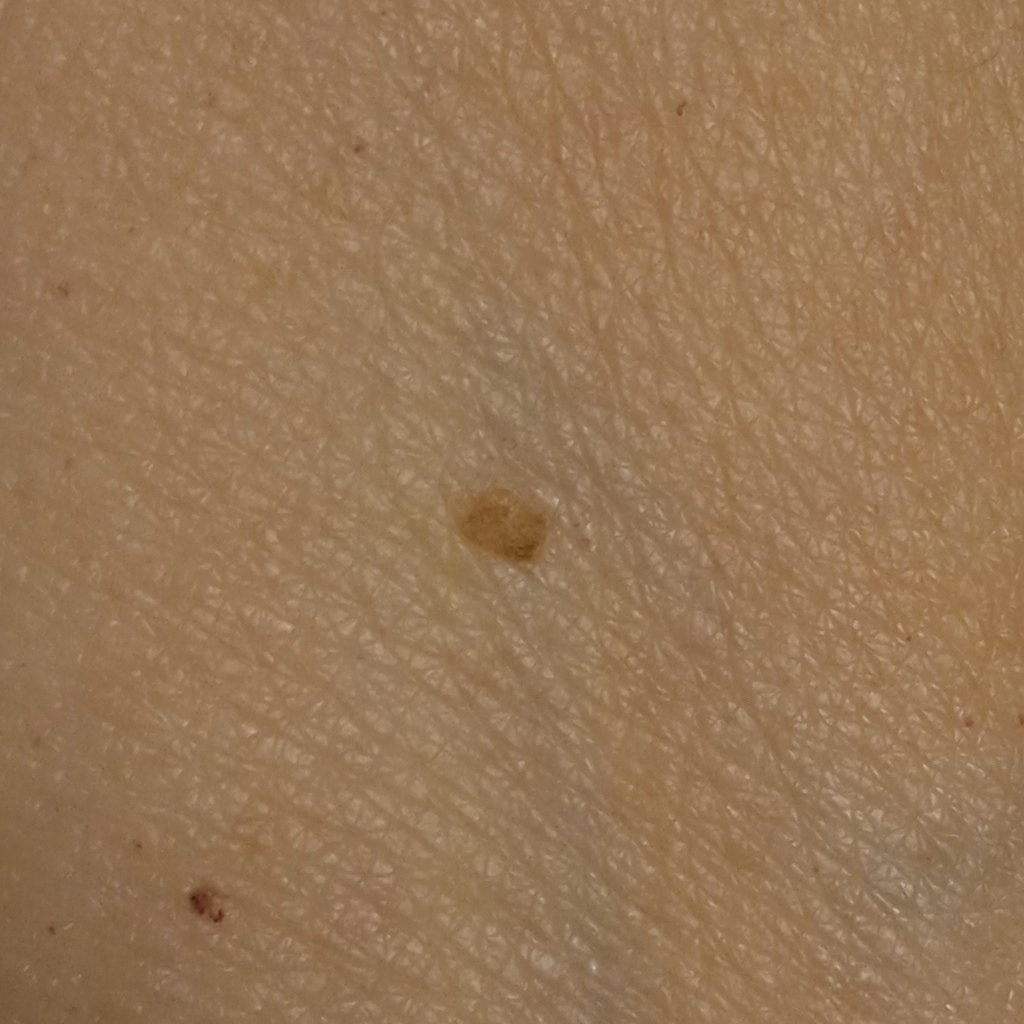The patient says their skin tans without first burning. By self-report, no immunosuppression and no family history of skin cancer. A female subject 67 years of age. Acquired for a research image collection, with no referral diagnosis. The lesion measures approximately 3.1 mm. The lesion was assessed as a seborrheic keratosis.